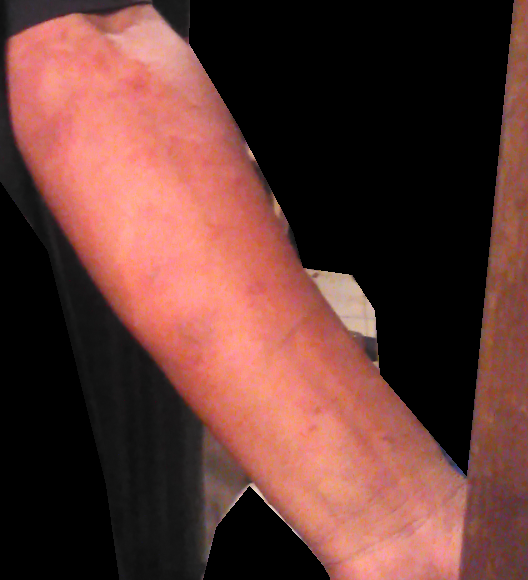shot type: at a distance | dermatologist impression: Hypersensitivity and Allergic Contact Dermatitis were considered with similar weight.